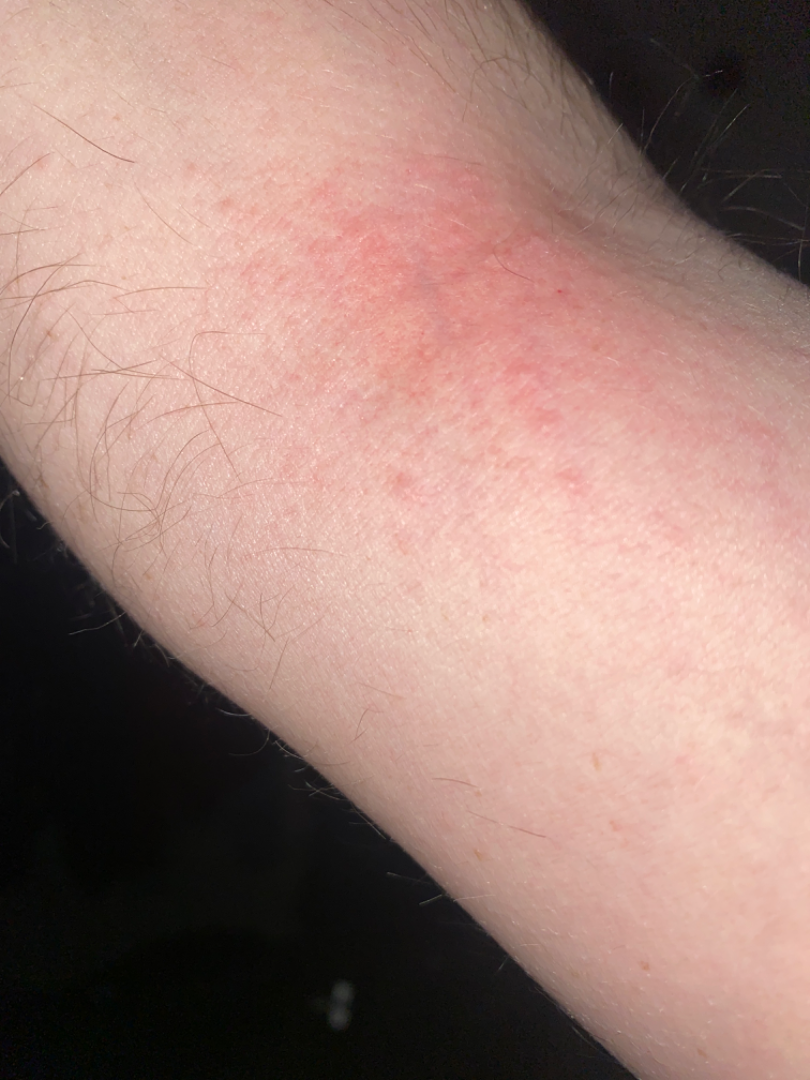Patient information: The contributor is 18–29, male. An image taken at an angle. The arm is involved. Review: On remote review of the image, the impression on review was Eczema.